The patient is skin type II; a female patient in their 80s; by history, tobacco use and prior malignancy (patient or family); a smartphone photograph of a skin lesion.
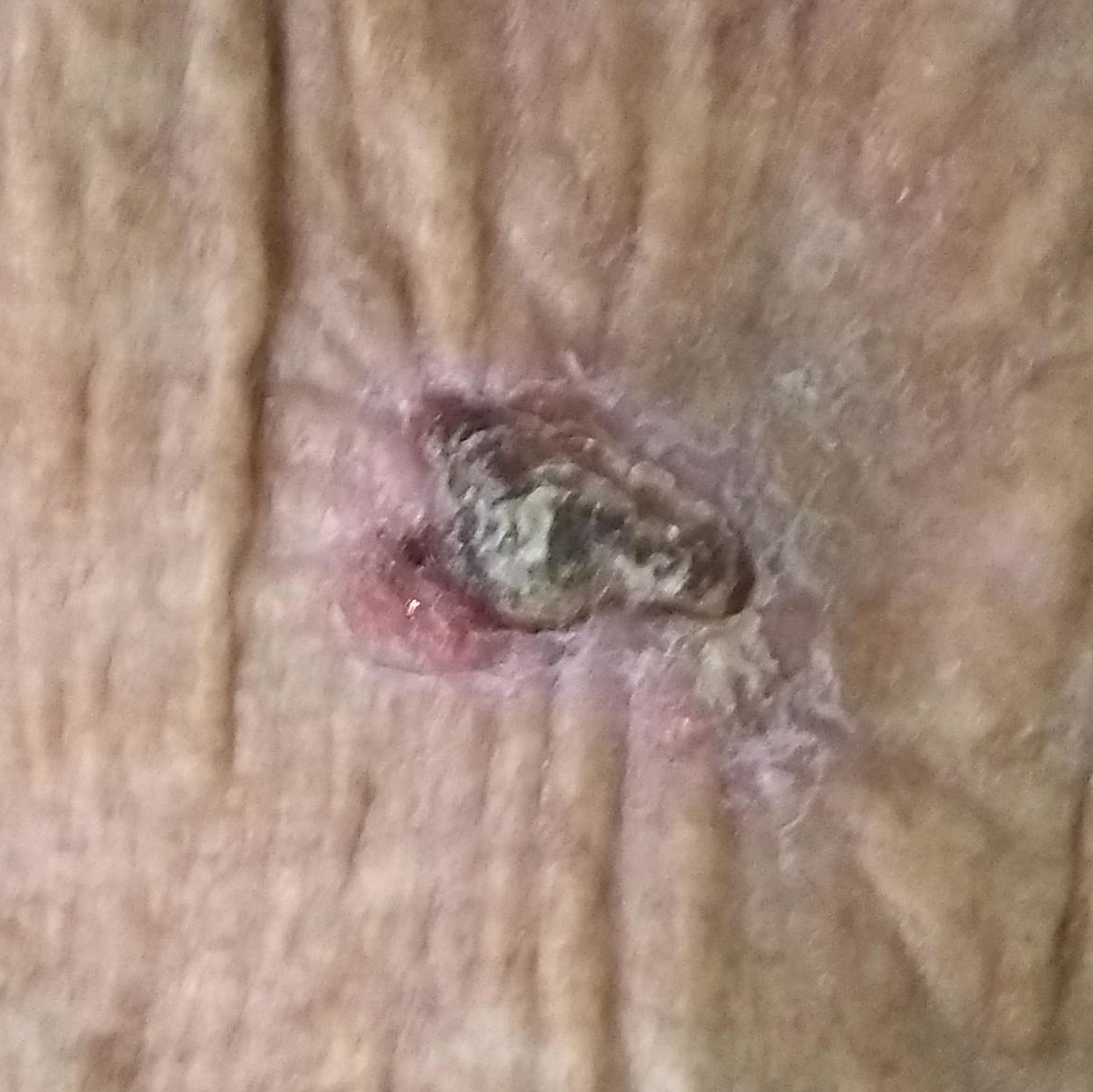– site — an arm
– diameter — 15x10 mm
– diagnosis — basal cell carcinoma (biopsy-proven)